A skin lesion imaged with a dermatoscope.
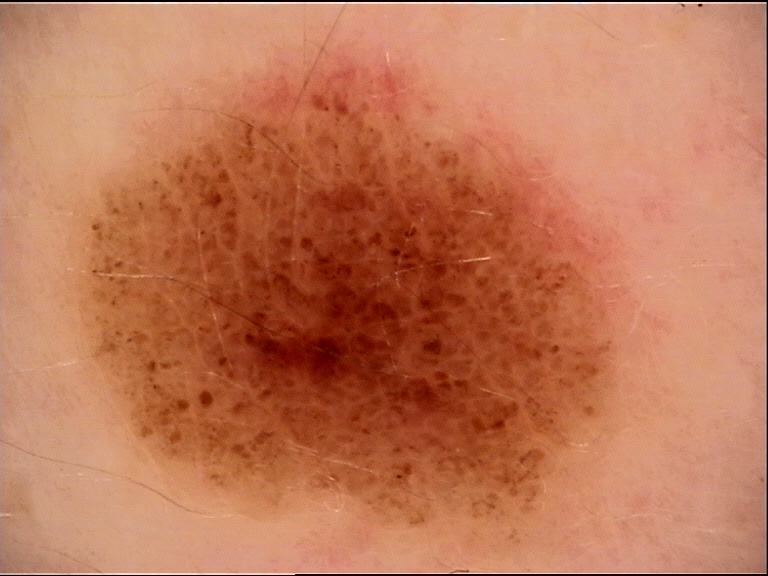The morphology is that of a banal lesion. Diagnosed as a junctional nevus.